This image was taken at an angle:
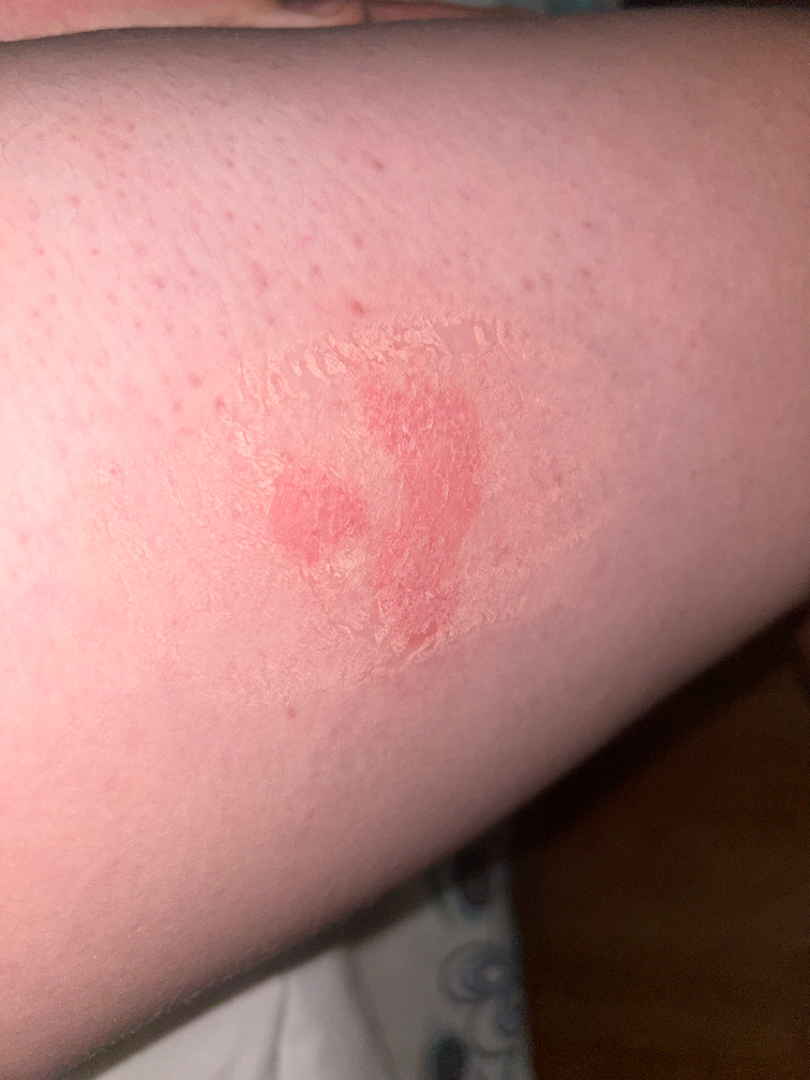<case>
<texture>raised or bumpy</texture>
<symptoms>itching</symptoms>
<patient_category>a rash</patient_category>
<duration>about one day</duration>
<differential>
  <tied_lead>Eczema, Allergic Contact Dermatitis, Irritant Contact Dermatitis</tied_lead>
</differential>
</case>